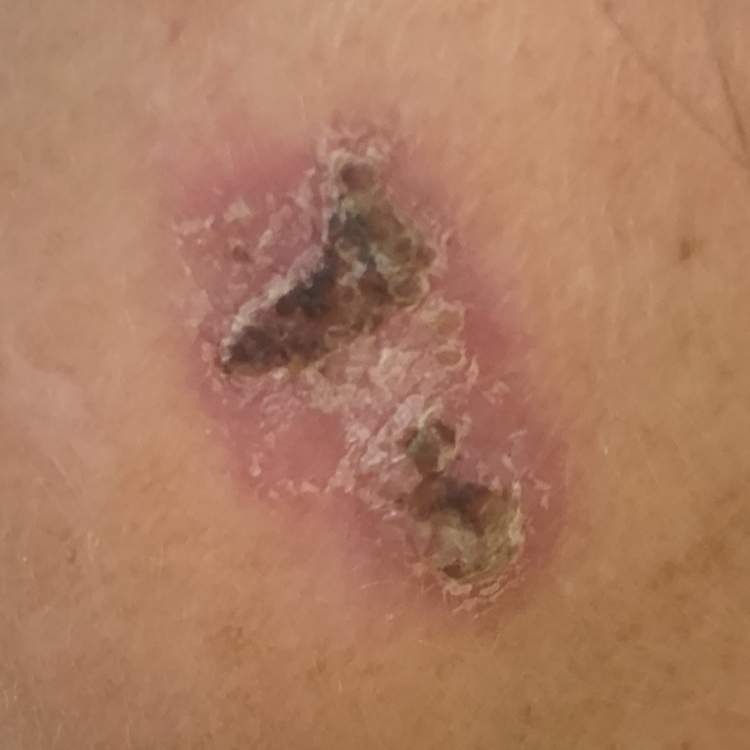Confirmed on histopathology as a basal cell carcinoma.